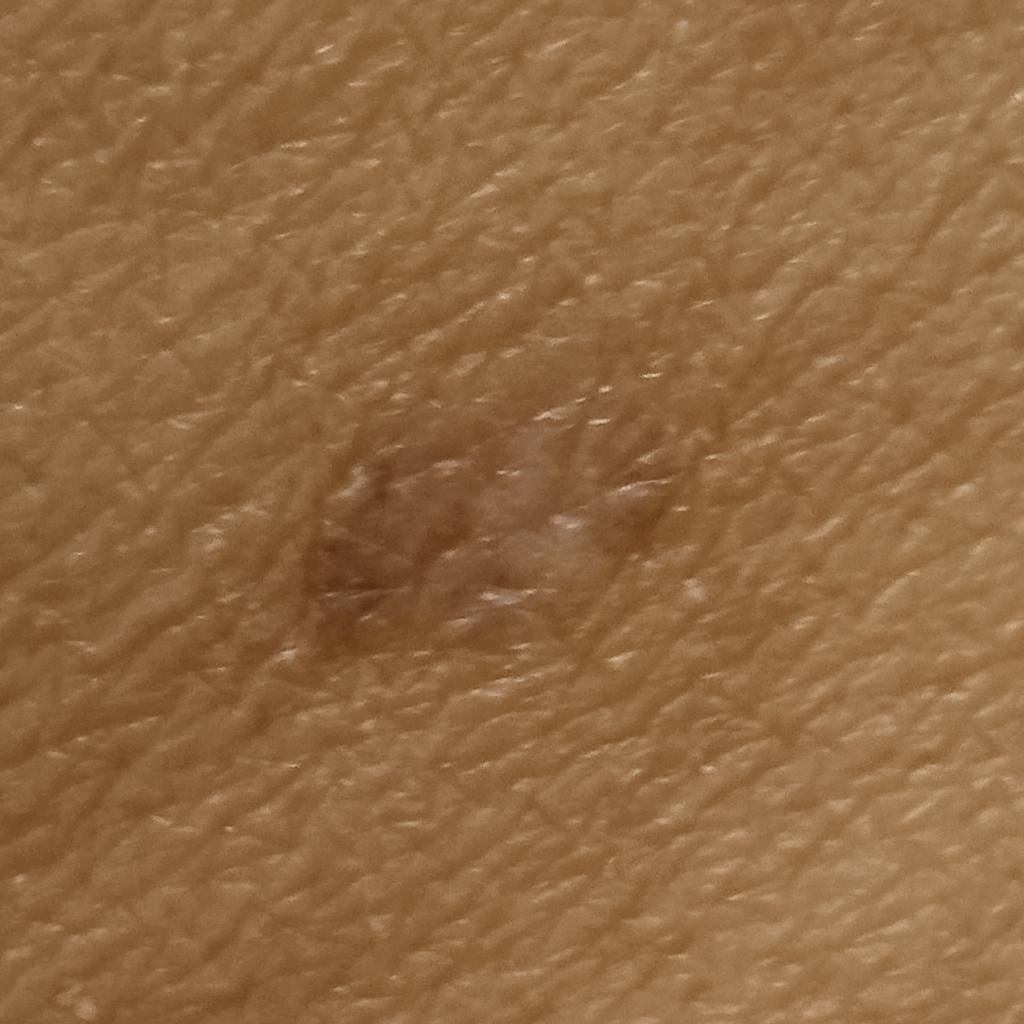Case summary: A female subject age 60. On a questionnaire the patient reported a personal history of cancer and a personal history of skin cancer. A clinical photograph showing a skin lesion. Few moles overall by the patient's own estimate. Located on the torso. Measuring roughly 3.4 mm. Conclusion: The lesion was assessed as a melanocytic nevus.